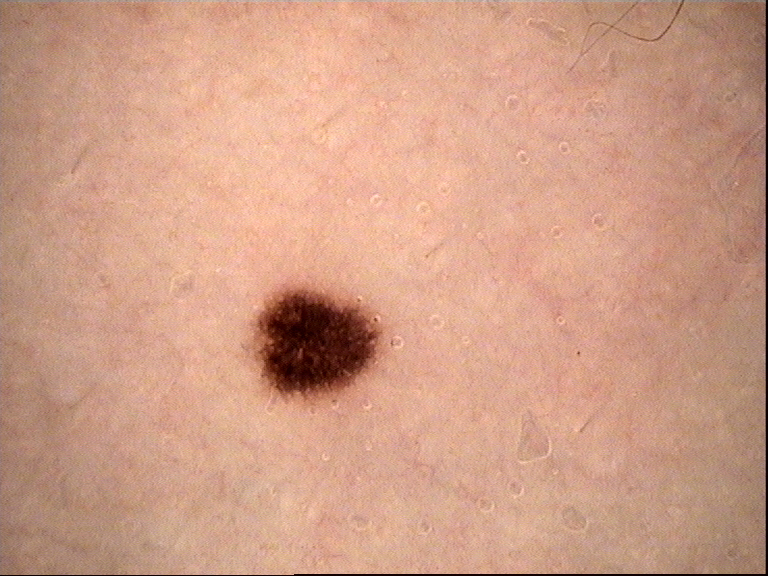diagnosis: dysplastic junctional nevus (expert consensus).